Located on the front of the torso, back of the torso and arm. A close-up photograph: 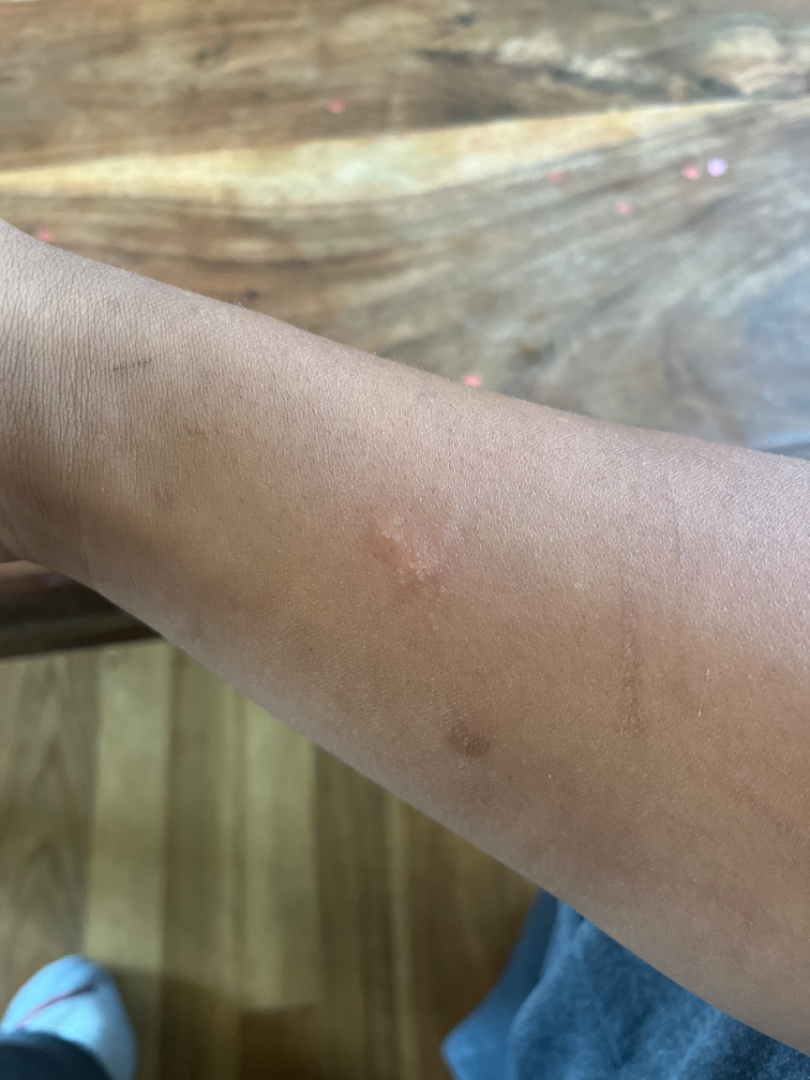| key | value |
|---|---|
| assessment | not assessable |